A female subject 79 years of age · history notes prior skin cancer (patient or family), pesticide exposure, prior malignancy (patient or family), and no alcohol use · recorded as Fitzpatrick II · a clinical photo of a skin lesion taken with a smartphone:
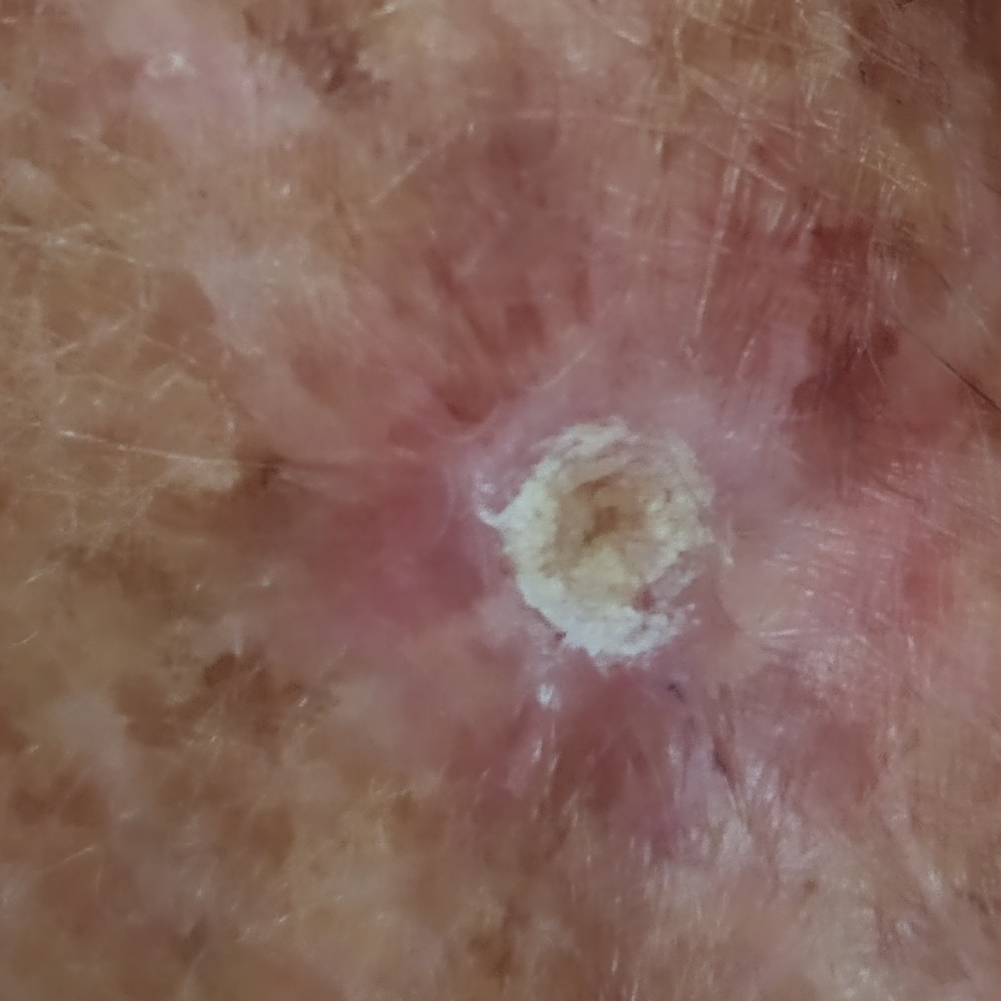| field | value |
|---|---|
| site | a forearm |
| diameter | approx. 15 × 13 mm |
| symptoms | elevation, itching |
| pathology | actinic keratosis (biopsy-proven) |